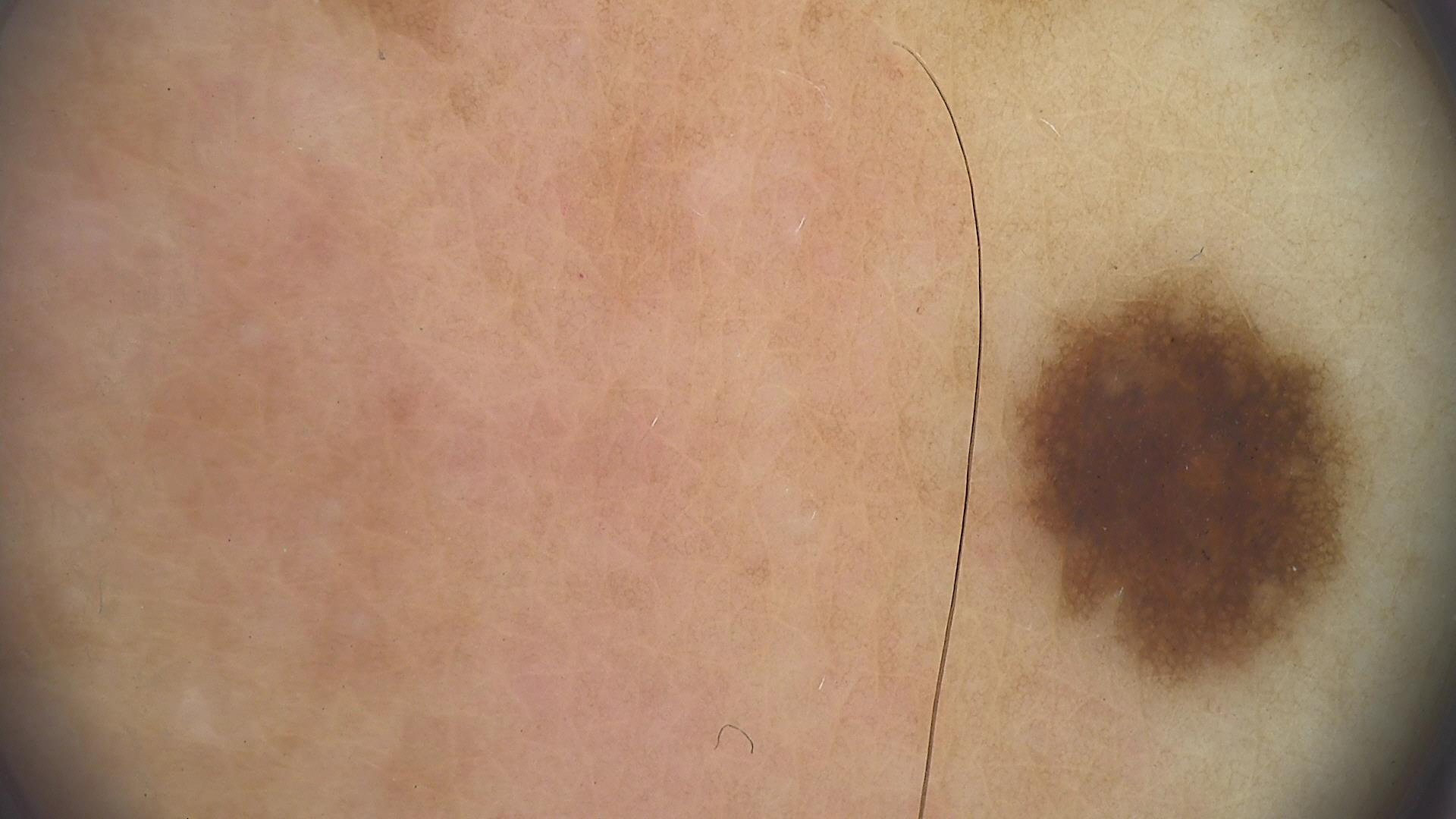| field | value |
|---|---|
| image type | dermatoscopy |
| class | dysplastic junctional nevus (expert consensus) |